This is a close-up image. The patient did not report lesion symptoms. Located on the head or neck — 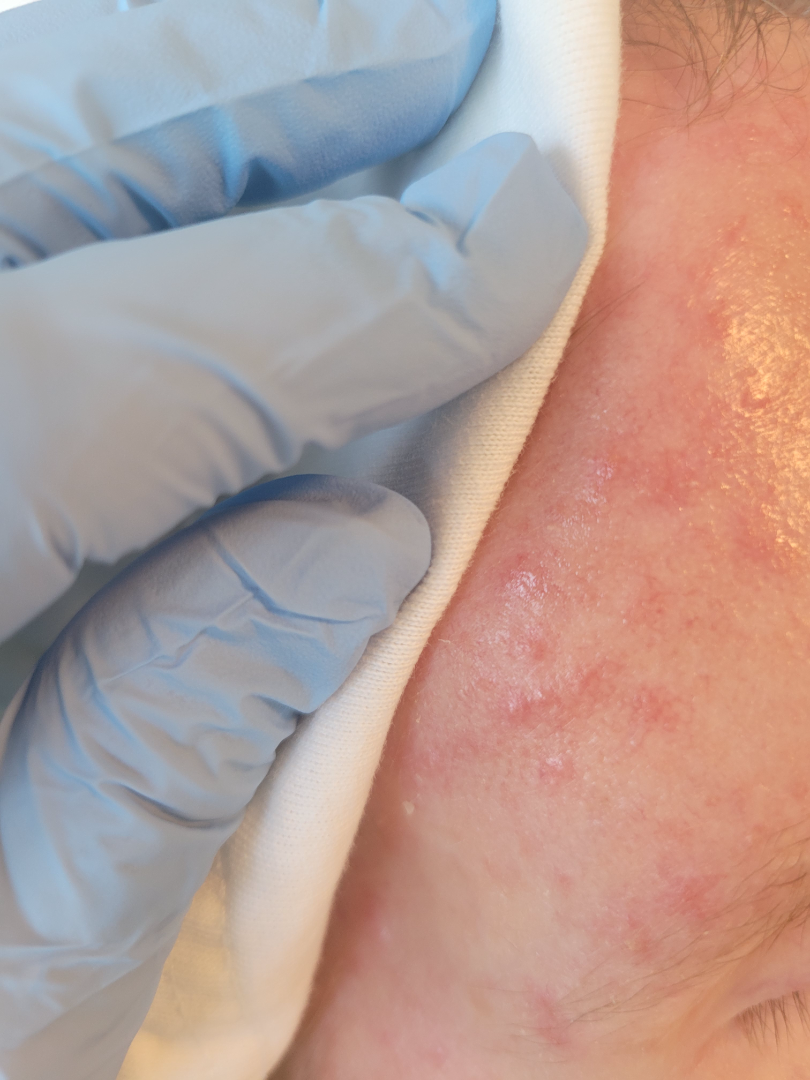Review: On dermatologist assessment of the image, Rosacea (67%); Acne (33%).